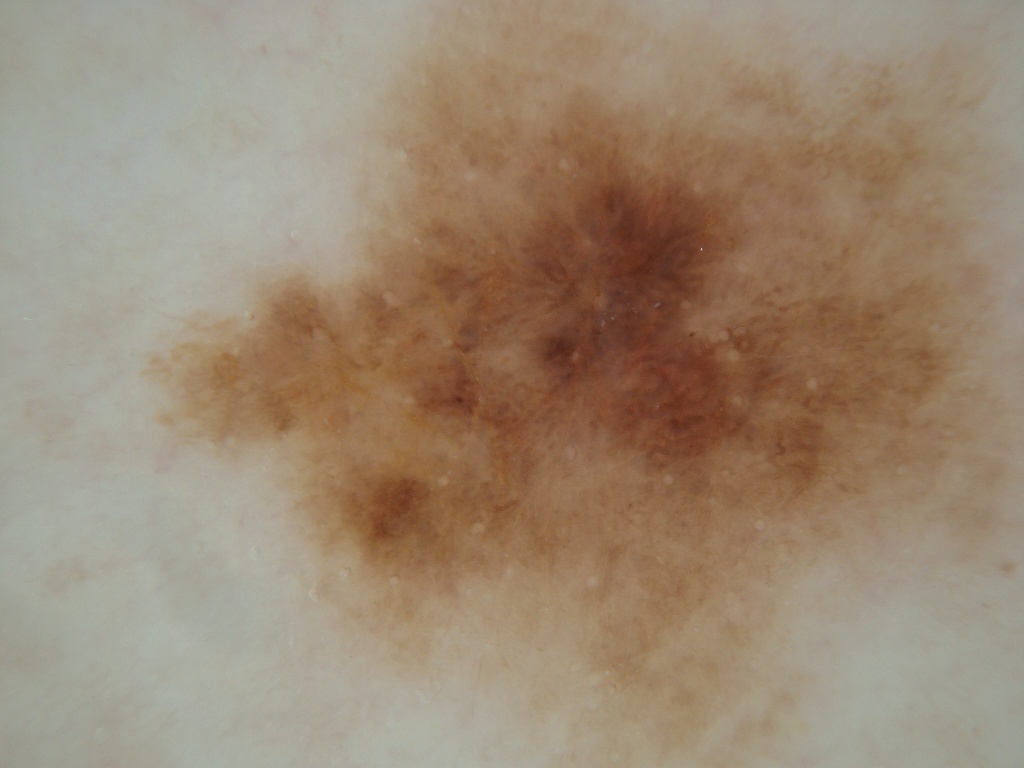Case summary:
– subject — female, approximately 65 years of age
– image type — dermatoscopic image of a skin lesion
– dermoscopic findings — globules and pigment network; absent: negative network, milia-like cysts, and streaks
– lesion margin — extends past the field edge
– location — bbox(145, 0, 1019, 763)
– assessment — a melanoma, a skin cancer